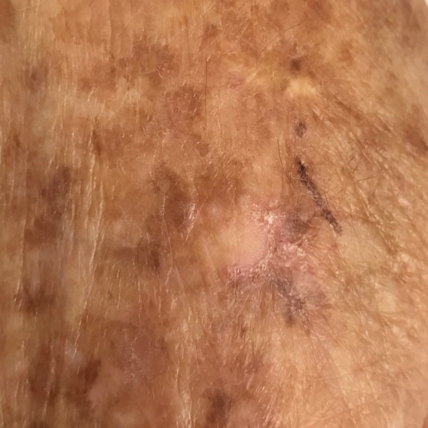Findings:
- subject · 73 years of age
- symptoms · itching
- impression · actinic keratosis (clinical consensus)